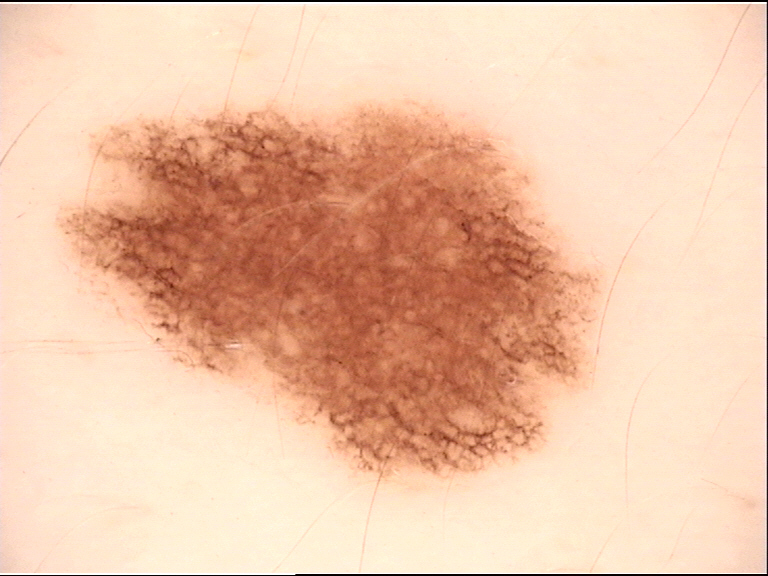assessment: dysplastic junctional nevus (expert consensus)